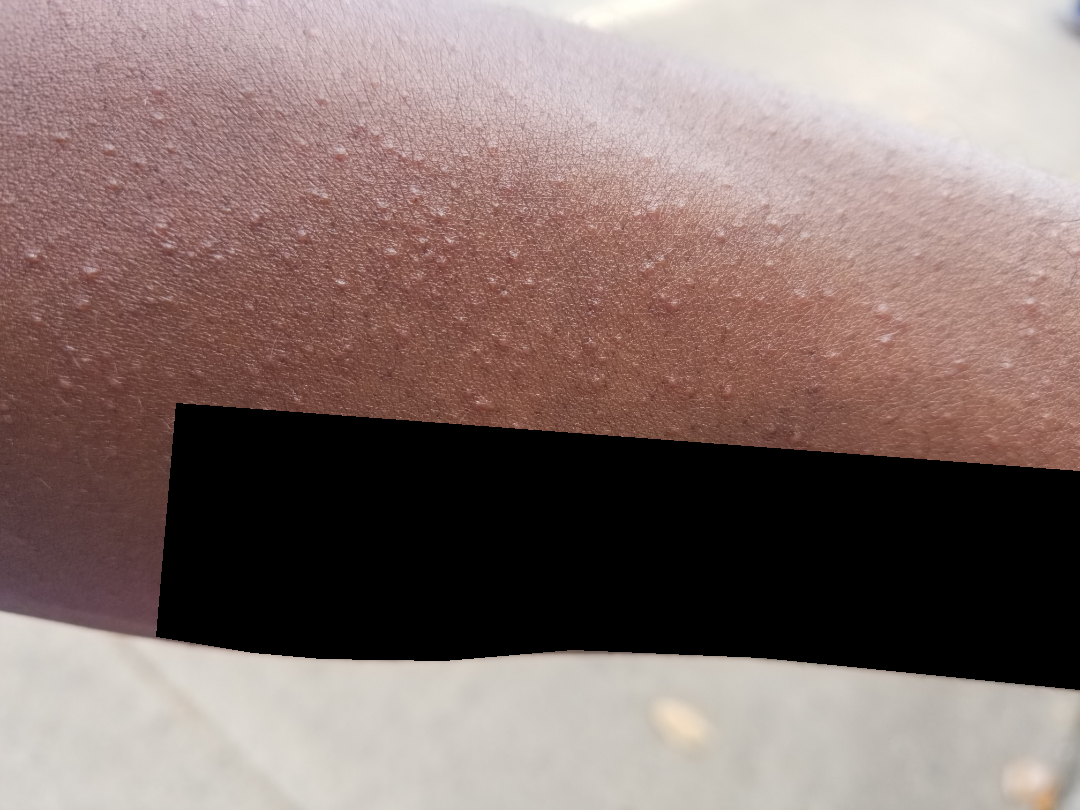Notes:
– texture: raised or bumpy
– framing: close-up
– lesion symptoms: itching
– duration: less than one week
– body site: palm, front of the torso and arm
– clinical impression: Miliaria, Folliculitis and Keratosis pilaris were considered with similar weight